This image was taken at a distance · reported duration is about one day · the lesion is associated with itching · self-categorized by the patient as a rash.
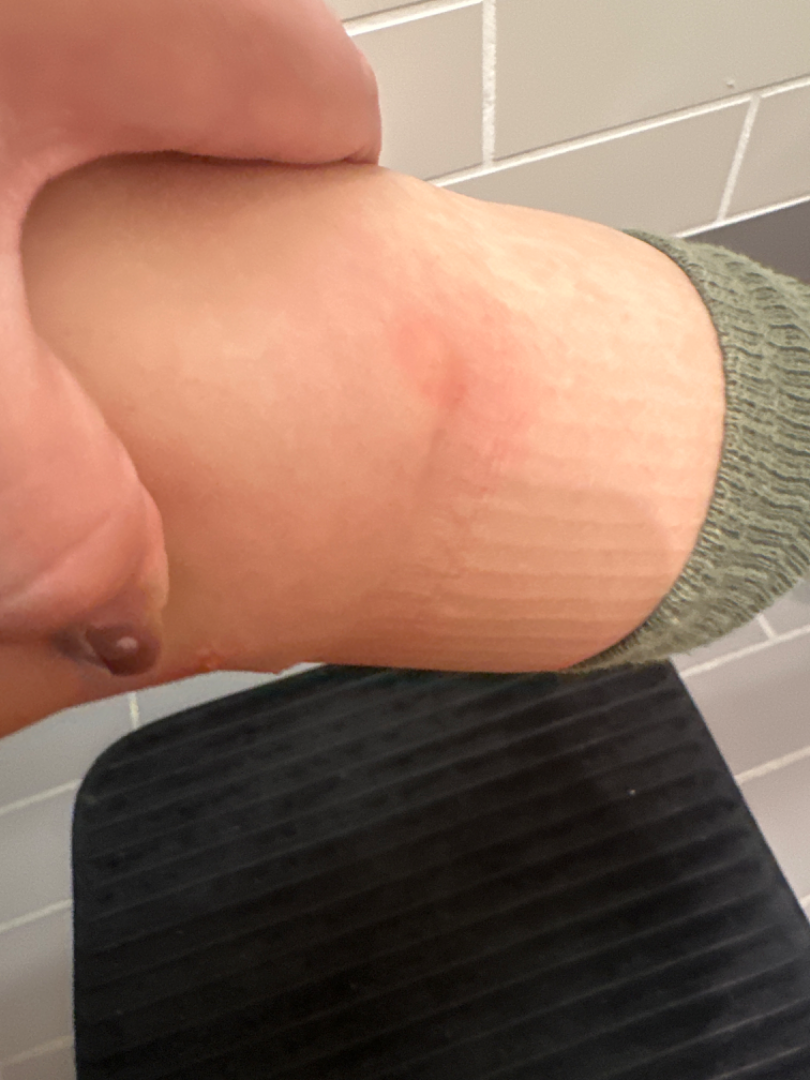| key | value |
|---|---|
| differential | Psoriasis (considered); Eczema (considered); Tinea (lower probability) |